The back of the torso is involved · this image was taken at an angle: 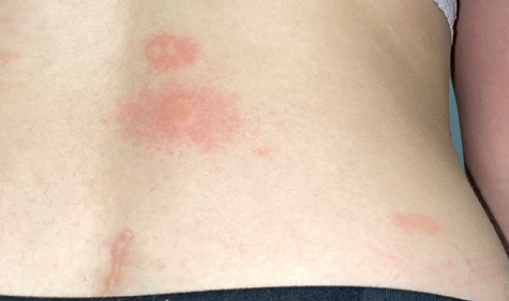The patient also reports mouth sores. The condition has been present for one to four weeks. Symptoms reported: bothersome appearance and itching. The lesion is described as raised or bumpy and rough or flaky. Urticaria (leading).